No relevant systemic symptoms. Located on the head or neck. Symptoms reported: bothersome appearance and itching. Self-categorized by the patient as a rash. A close-up photograph. Texture is reported as raised or bumpy. Reported duration is one to four weeks.
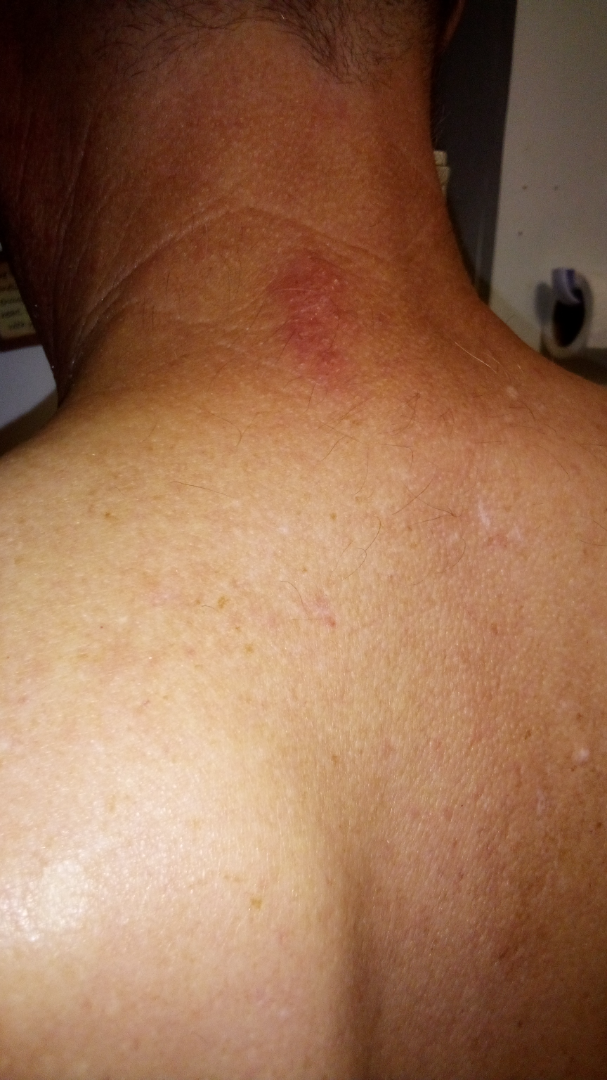assessment: could not be assessed.